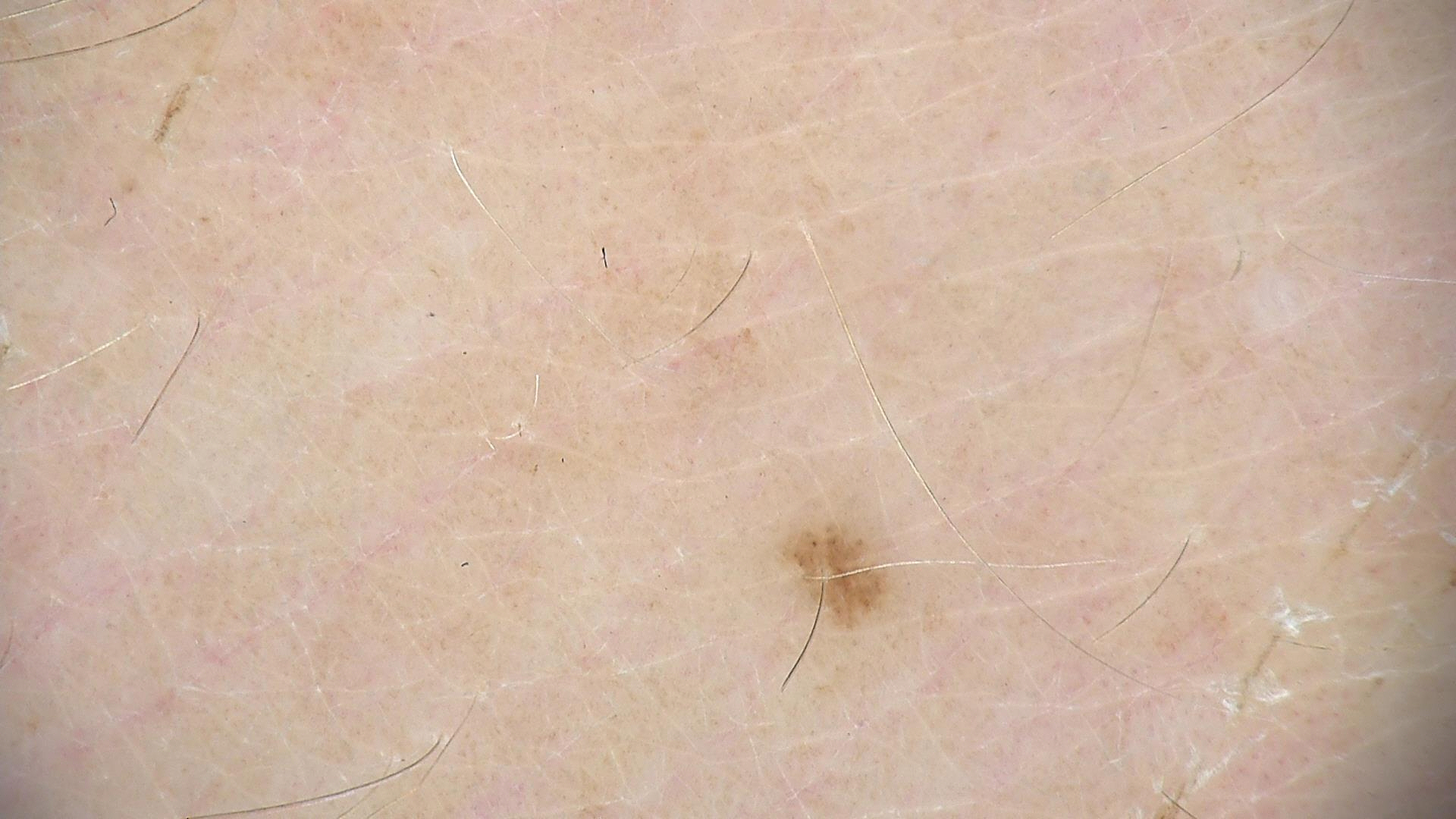class: dysplastic junctional nevus (expert consensus).